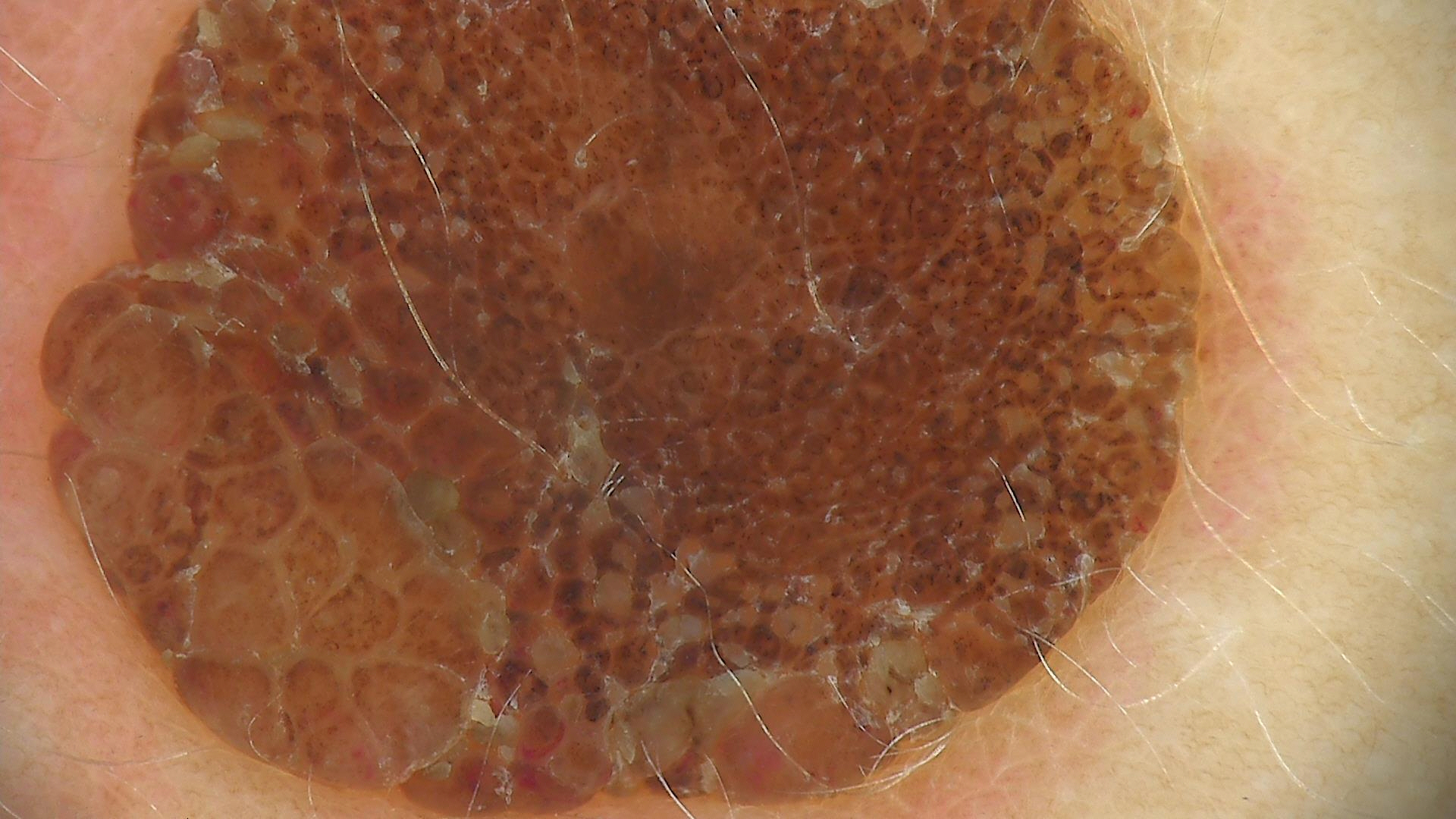lesion type — banal | class — dermal nevus (expert consensus).